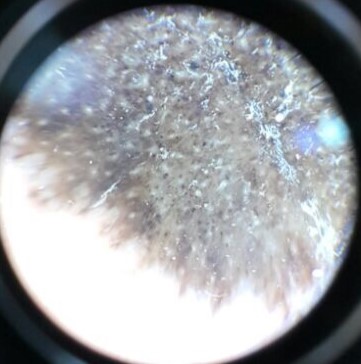Q: What kind of image is this?
A: dermoscopy
Q: How is the lesion classified?
A: banal
Q: What is this lesion?
A: congenital compound nevus (expert consensus)